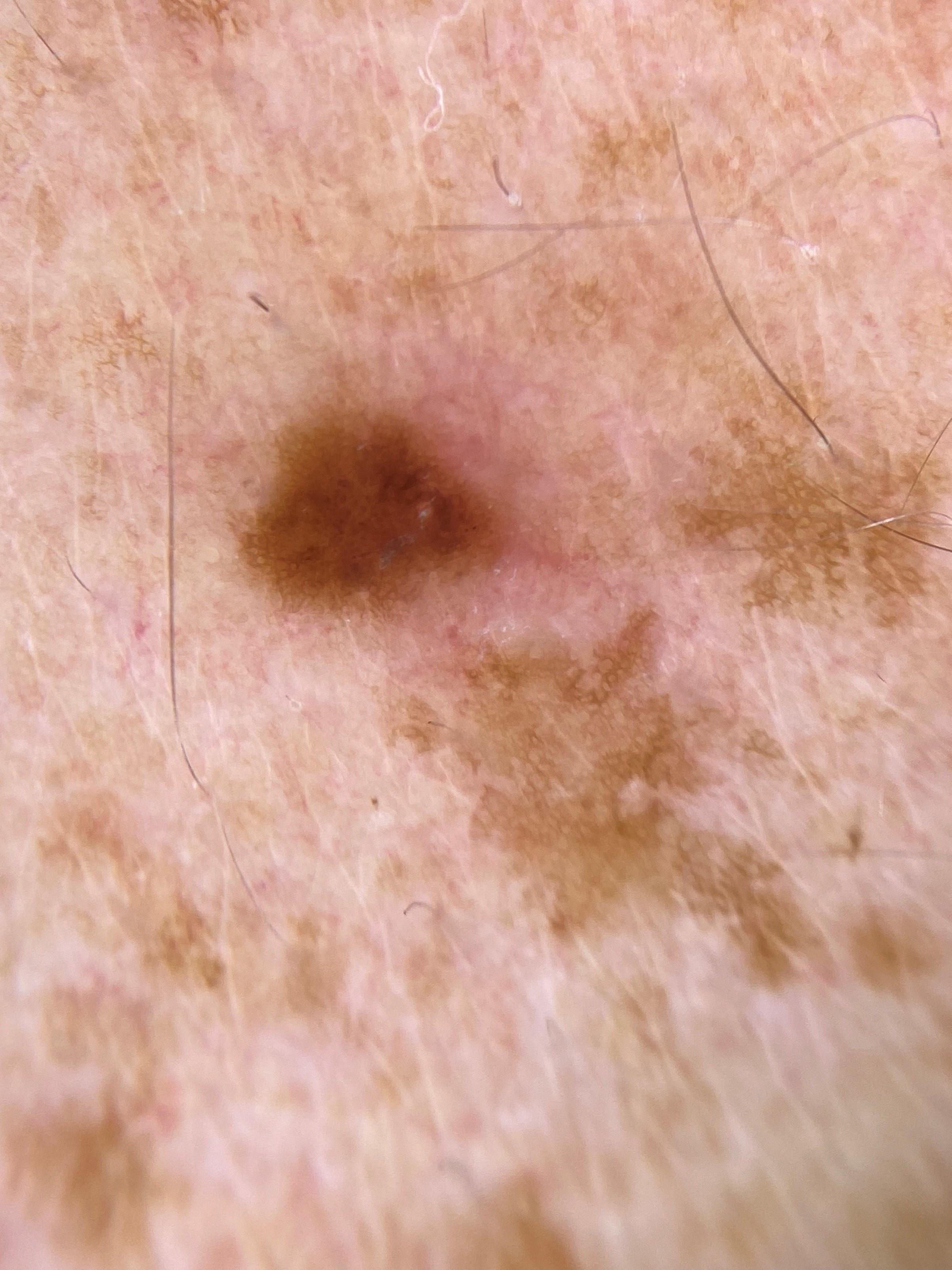Contact-polarized dermoscopy of a skin lesion. The chart records no previous melanoma and no first-degree relative with melanoma. A male subject about 30 years old. Recorded as Fitzpatrick skin type II. Located on the trunk, specifically the posterior trunk. The clinical assessment was a benign, melanocytic lesion — a nevus.